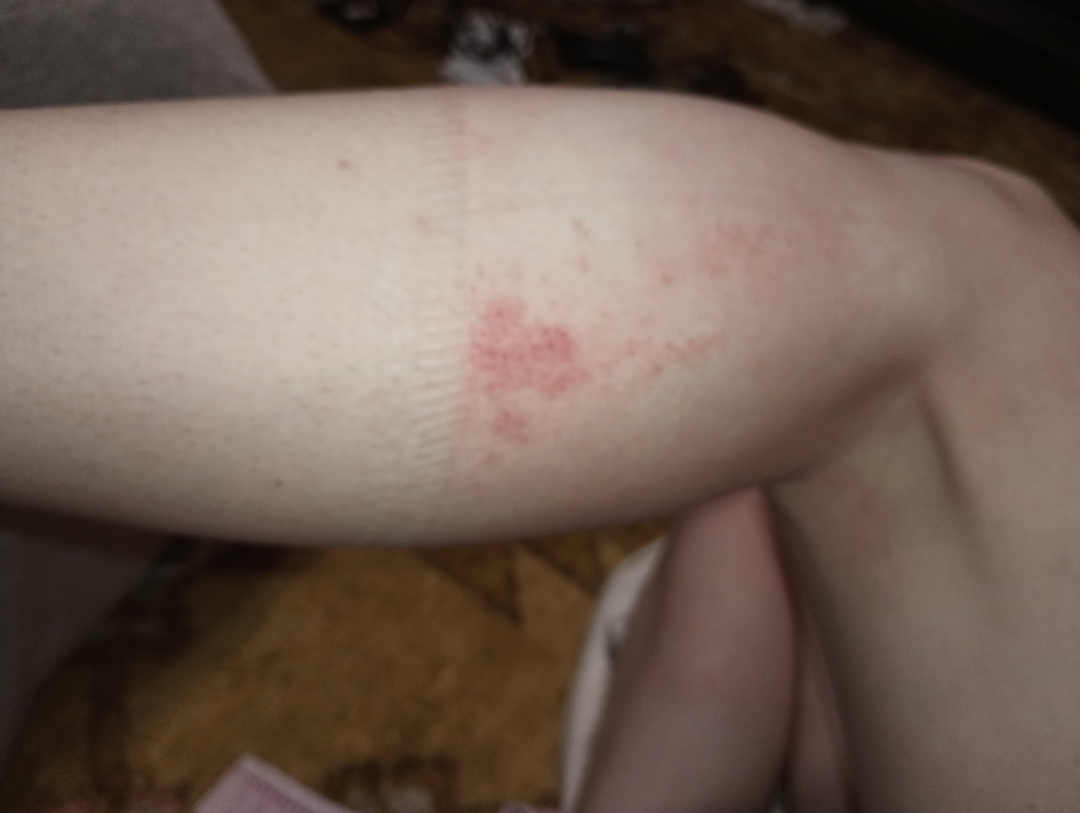The skin condition could not be confidently assessed from this image.